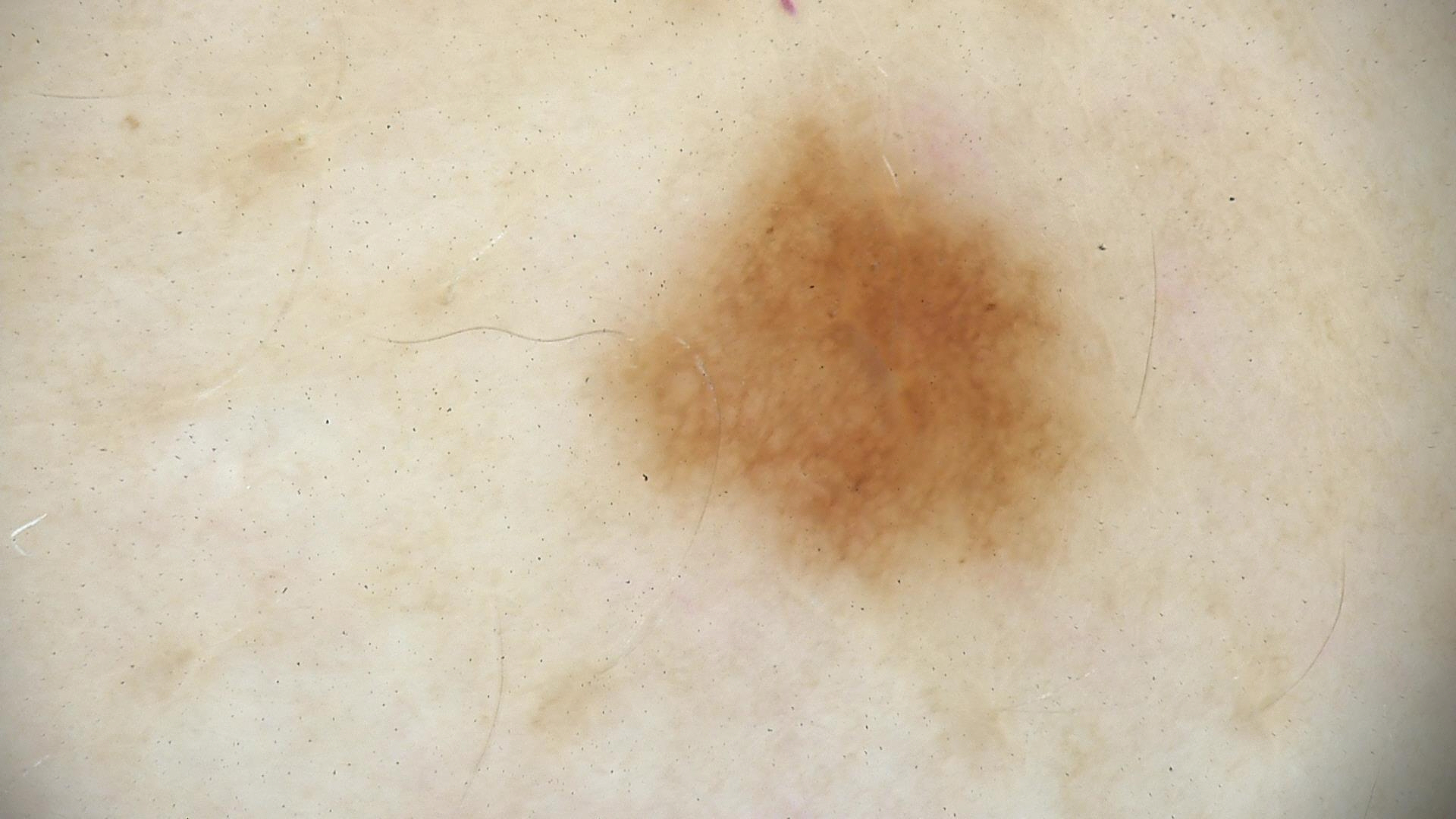diagnostic label: dysplastic junctional nevus (expert consensus)